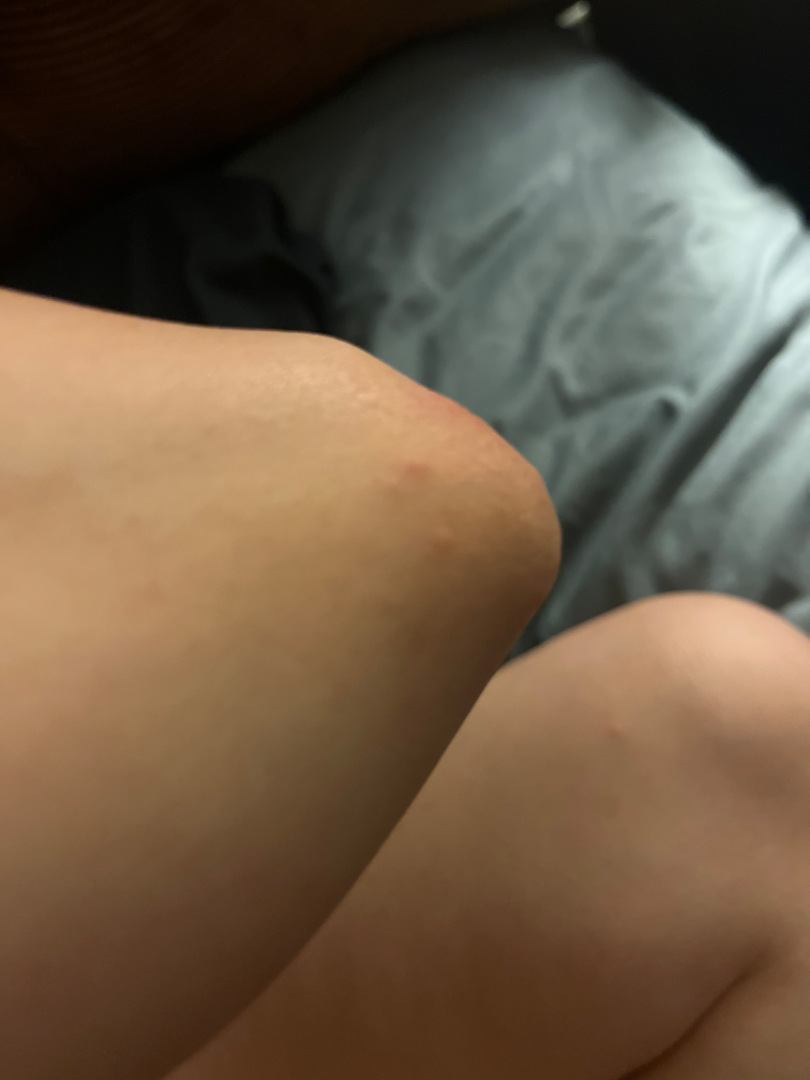The photograph was taken at an angle. The subject is 30–39, female. Located on the arm and palm. Most consistent with Scabies; also raised was Eczema.